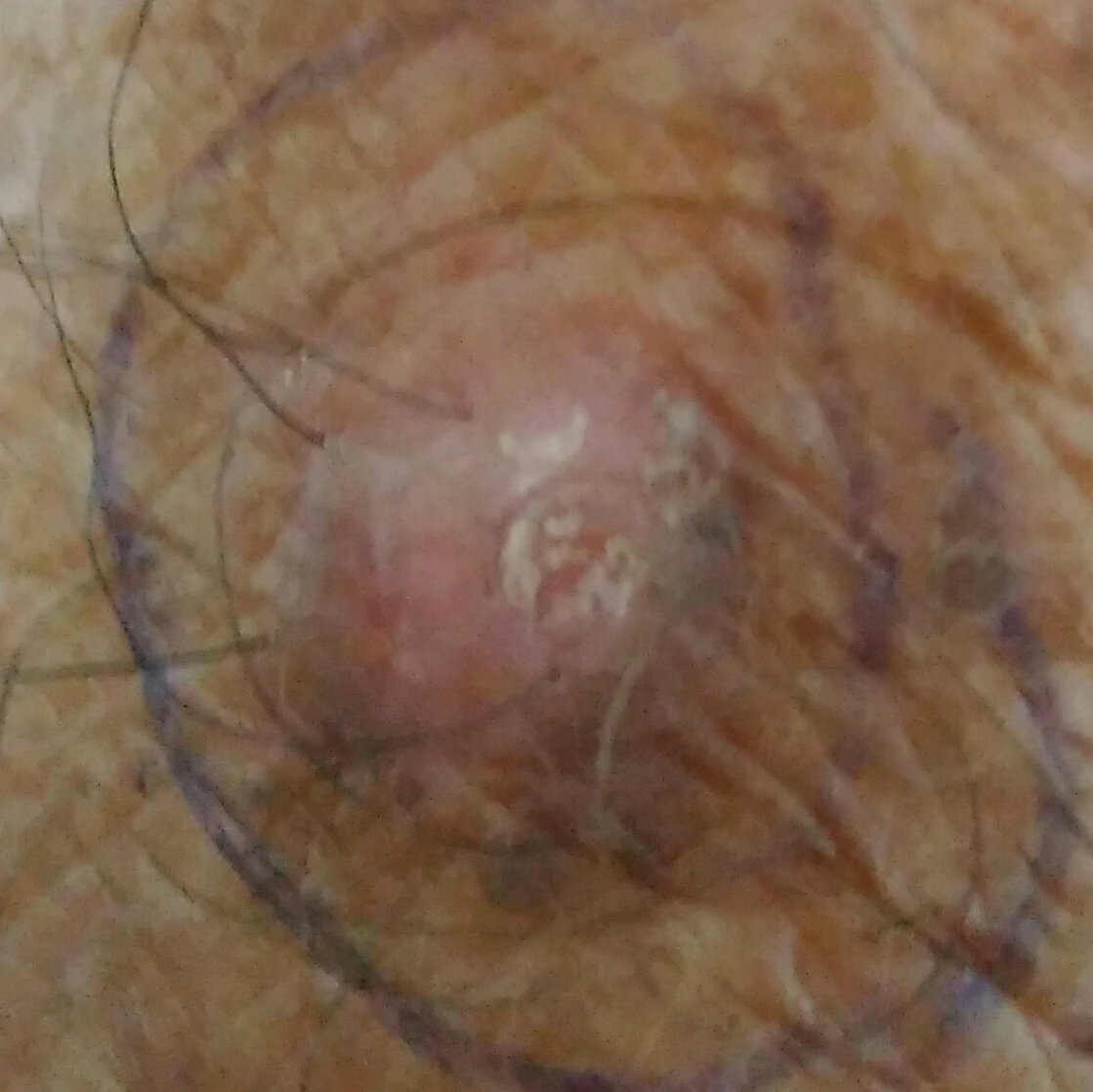A clinical photograph showing a skin lesion. A male subject age 90. The lesion is on a forearm. The patient describes that the lesion hurts and is elevated. Histopathological examination showed a squamous cell carcinoma.